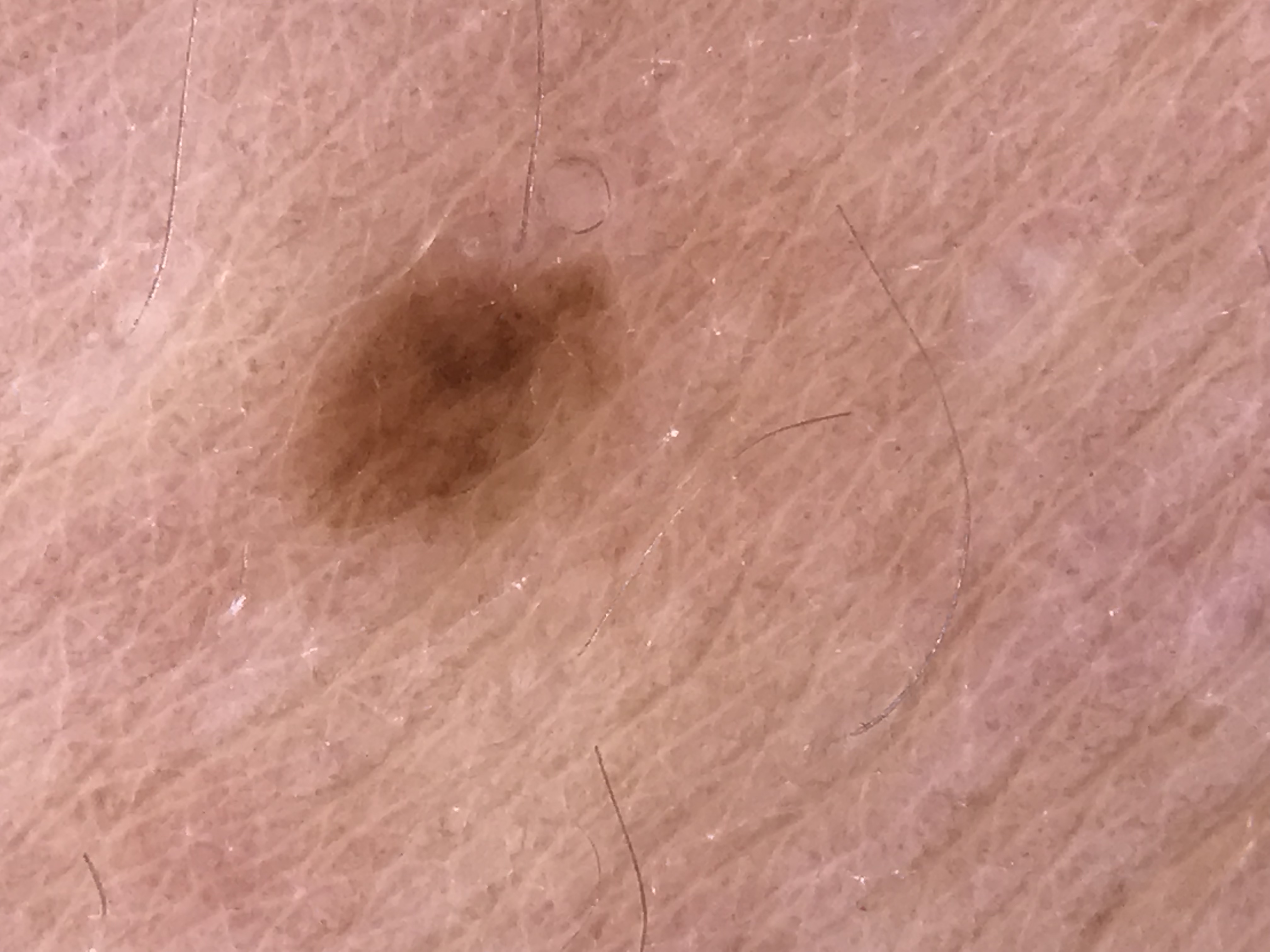Findings:
A dermoscopic image of a skin lesion.
Conclusion:
The diagnostic label was a banal lesion — a junctional nevus.